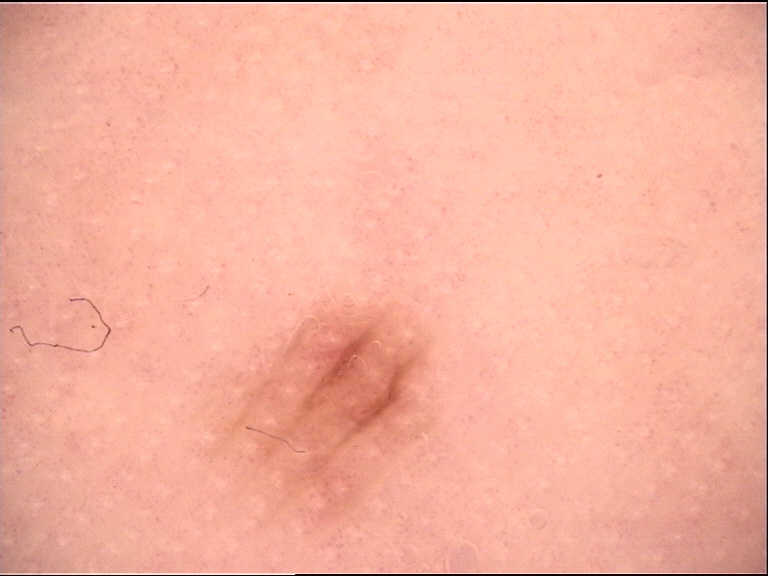Findings:
A dermoscopic close-up of a skin lesion.
Conclusion:
Classified as an acral dysplastic junctional nevus.